A dermoscopic photograph of a skin lesion:
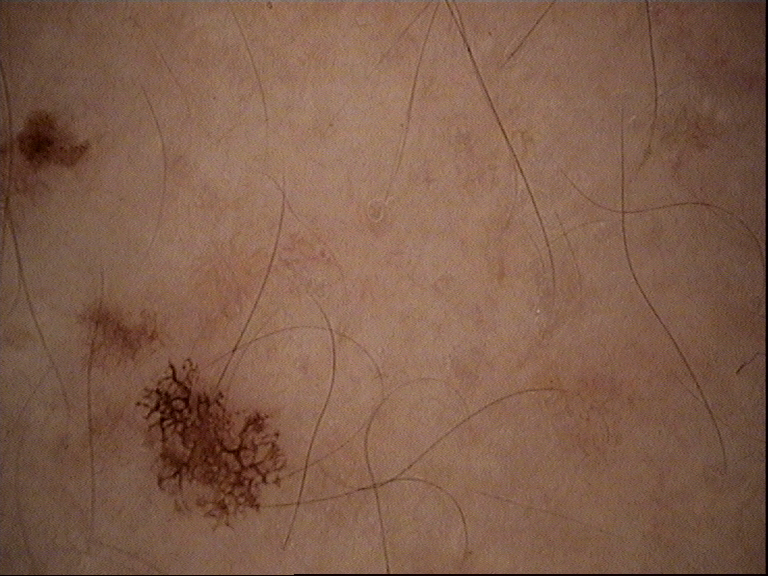Consistent with a benign lesion — a dysplastic junctional nevus.